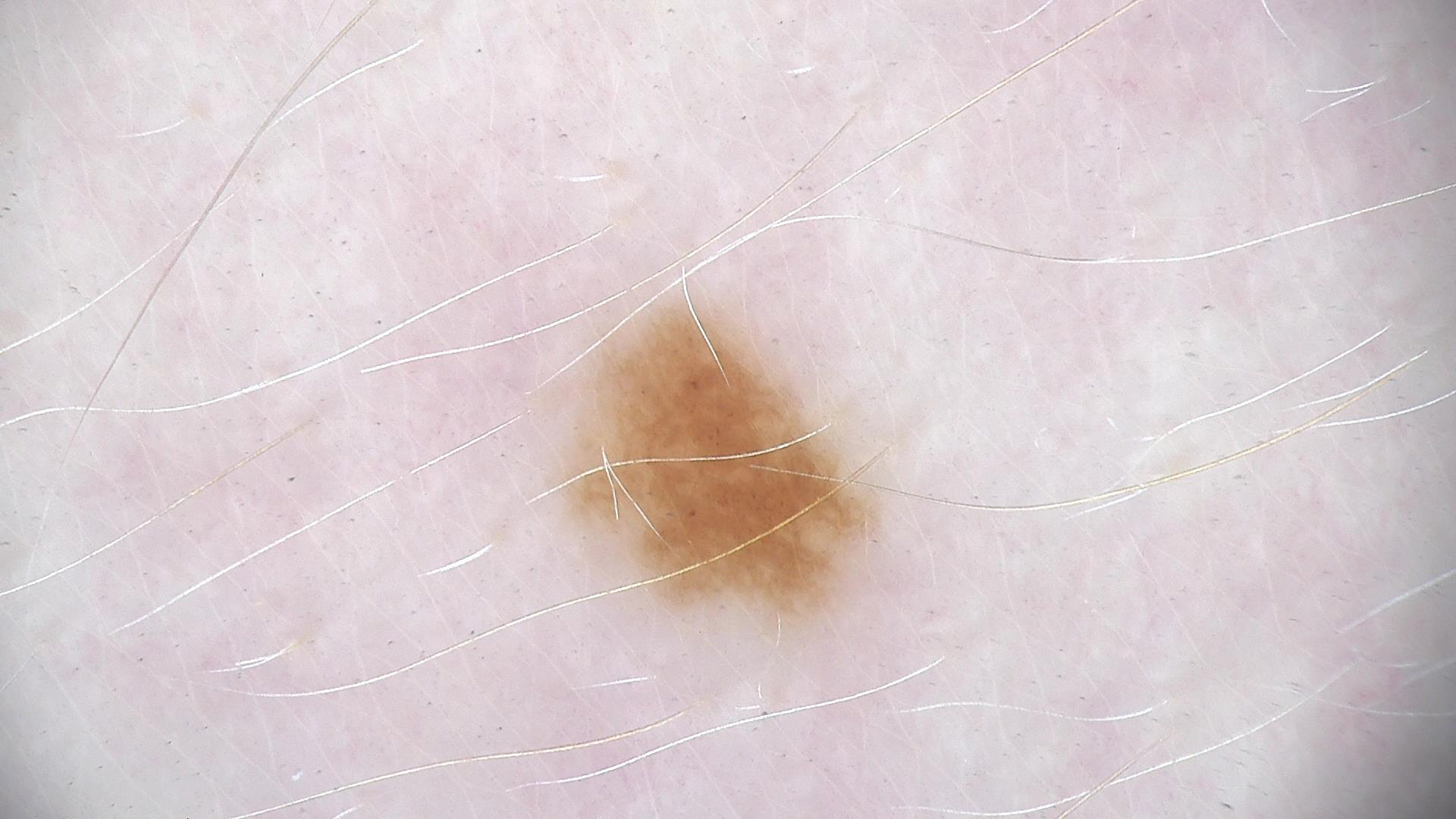image = dermoscopy | assessment = dysplastic junctional nevus (expert consensus).